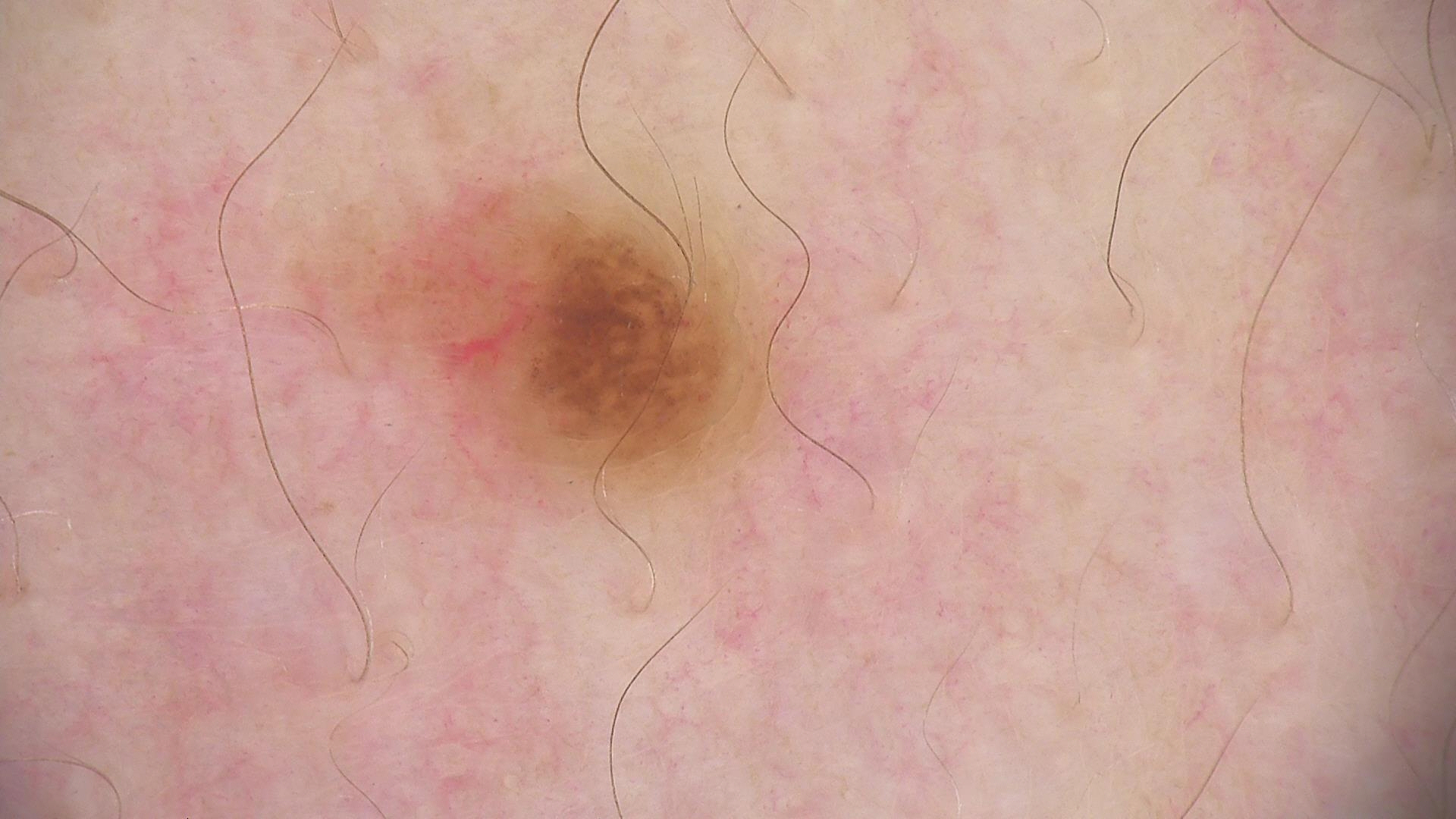{
  "diagnosis": {
    "name": "compound nevus",
    "code": "cb",
    "malignancy": "benign",
    "super_class": "melanocytic",
    "confirmation": "expert consensus"
  }
}